Dermoscopy of a skin lesion; a female patient, aged 38 to 42 — 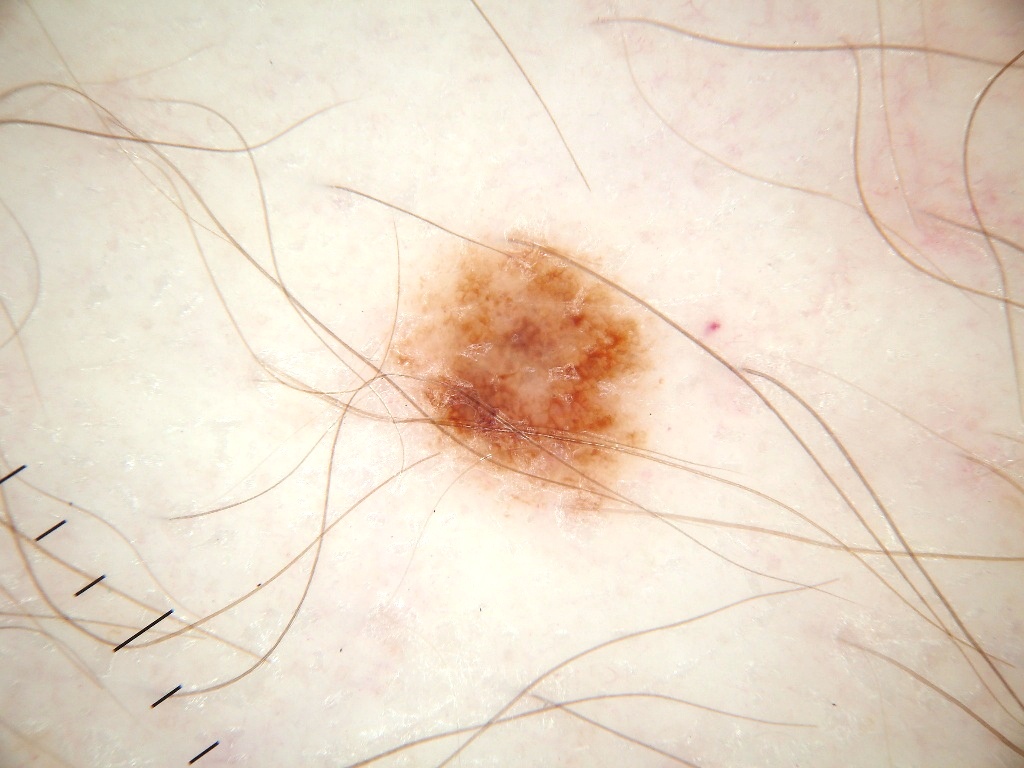Lesion location: x1=345 y1=217 x2=680 y2=544. Dermoscopically, the lesion shows pigment network, with no negative network, globules, milia-like cysts, or streaks. A mid-sized lesion within the field. The lesion was assessed as a melanocytic nevus.